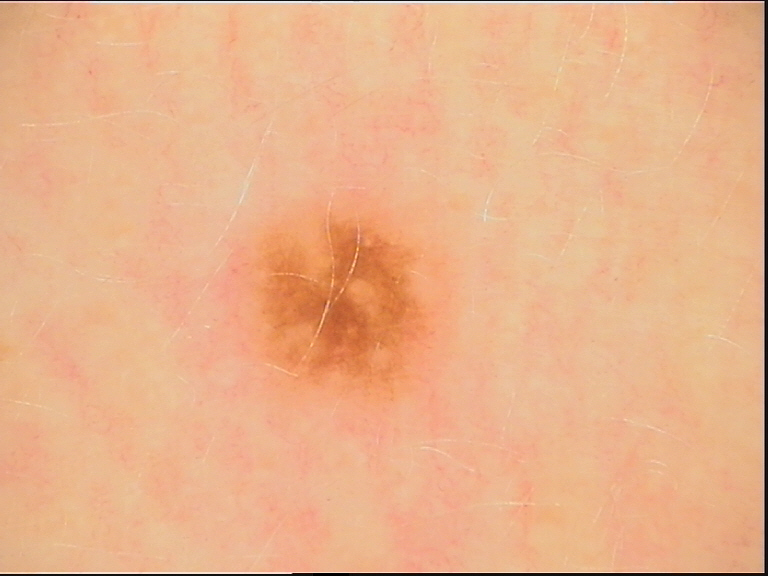The diagnostic label was a dysplastic junctional nevus.